Dermoscopy of a skin lesion. The subject is a female in their mid- to late 40s: 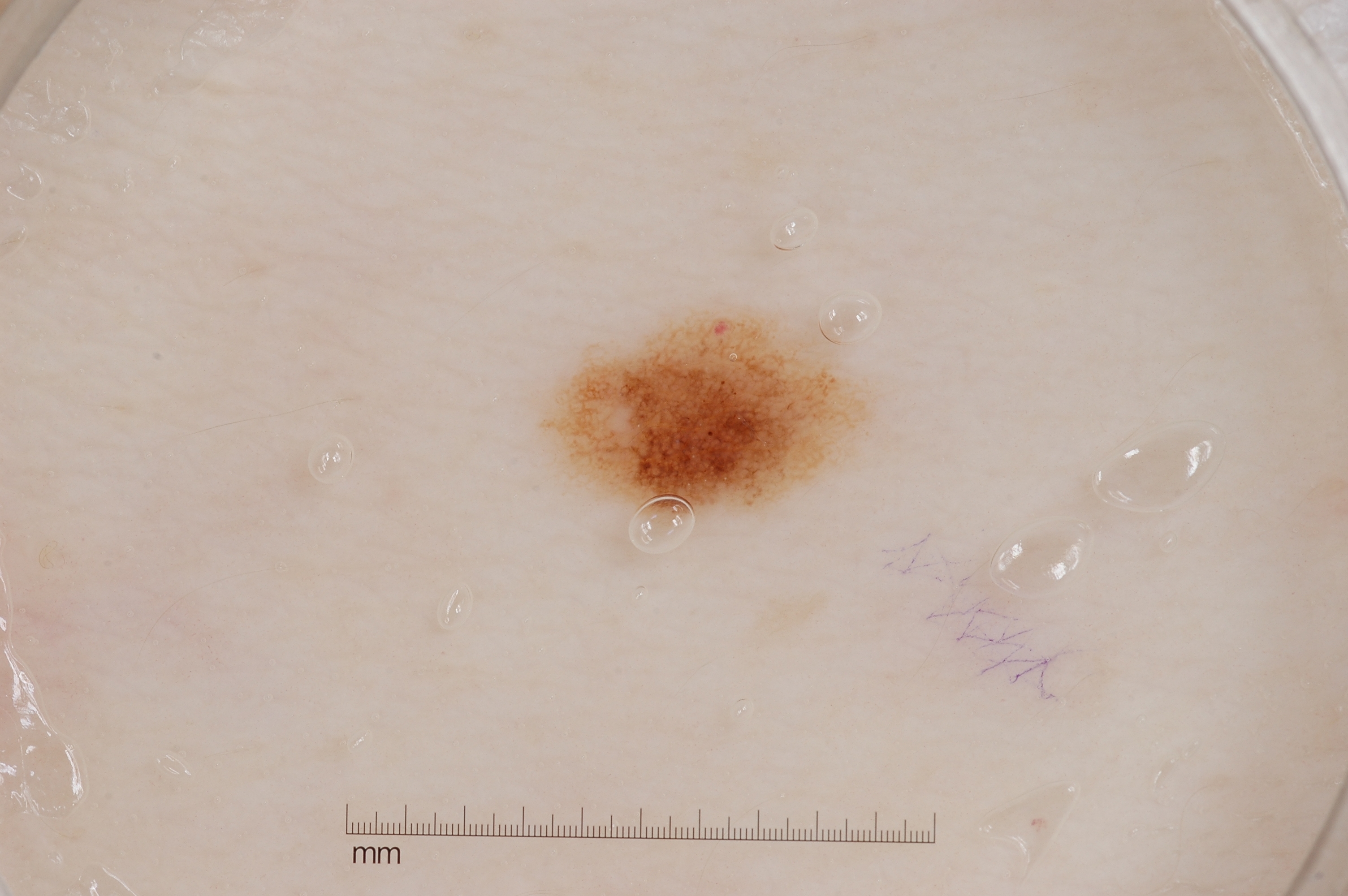The lesion takes up about 4% of the image.
In (x1, y1, x2, y2) order, the lesion spans 537, 306, 875, 523.
Dermoscopy demonstrates milia-like cysts and pigment network.
Clinically diagnosed as a melanocytic nevus, a benign skin lesion.